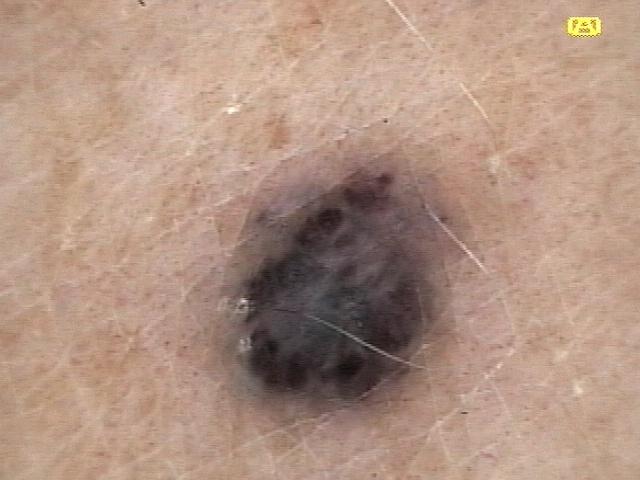Q: Patient demographics?
A: male, aged approximately 70
Q: How was this image acquired?
A: dermoscopy
Q: Where on the body is the lesion?
A: the trunk
Q: What was the clinical impression?
A: vascular lesion